The contributor is 18–29, male · the photograph is a close-up of the affected area:
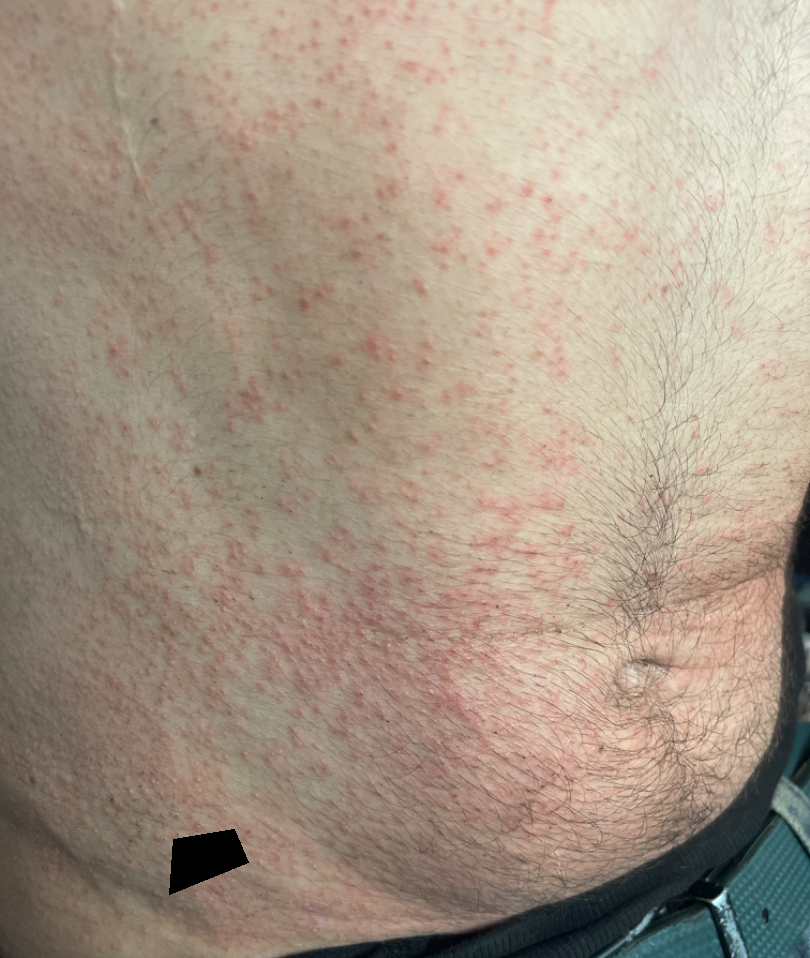clinical impression = favoring Drug Rash; the differential also includes Viral Exanthem; a remote consideration is Hypersensitivity.